Close-up view · located on the arm — 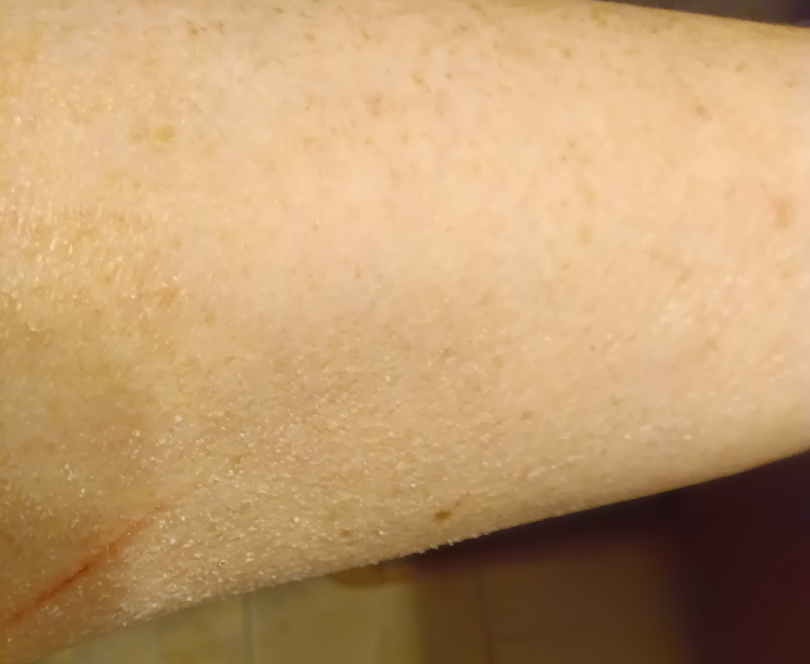  assessment: unable to determine
  texture: flat
  duration: less than one week
  systemic_symptoms: shortness of breath
  symptoms:
    - itching
    - enlargement